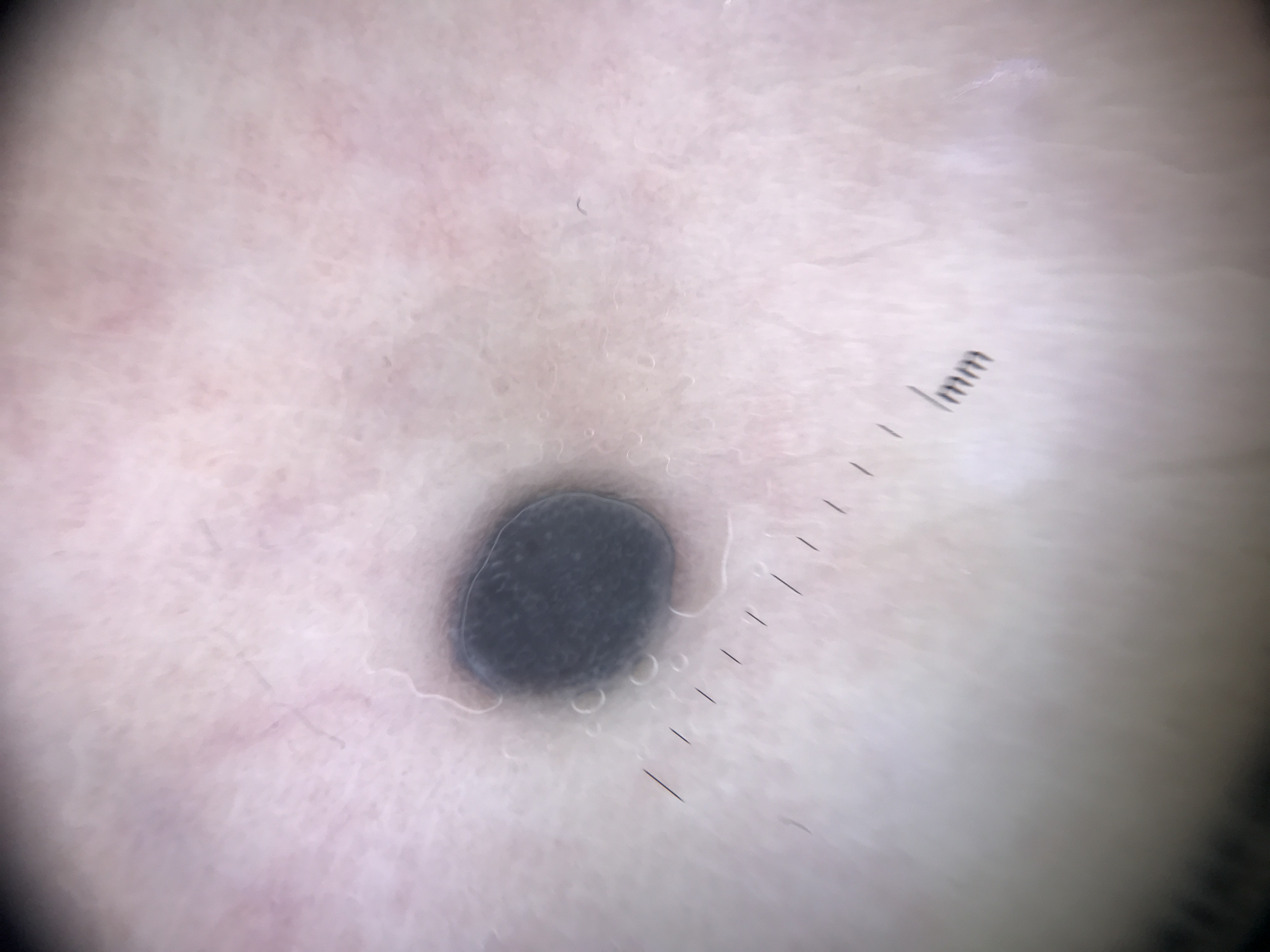A dermoscopic close-up of a skin lesion.
The diagnostic label was a blue nevus.